A skin lesion imaged with a dermatoscope:
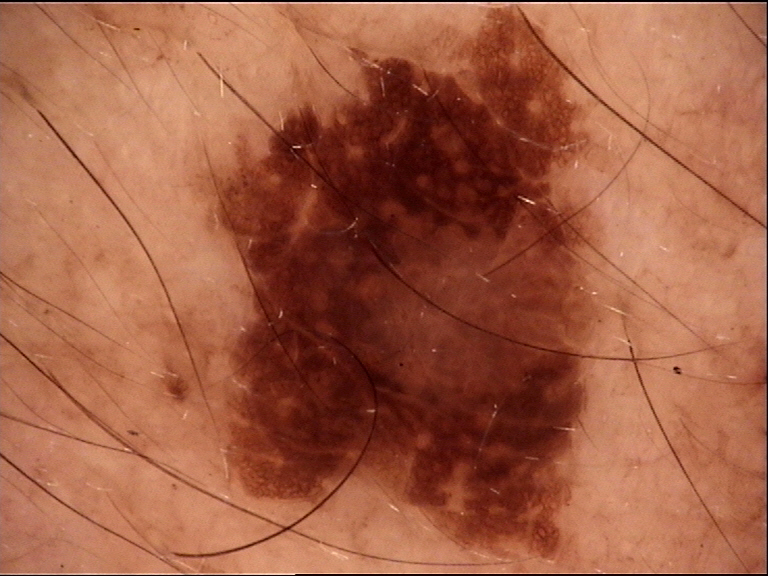diagnostic label: lentigo maligna (biopsy-proven)